The photograph is a close-up of the affected area. The affected area is the head or neck — 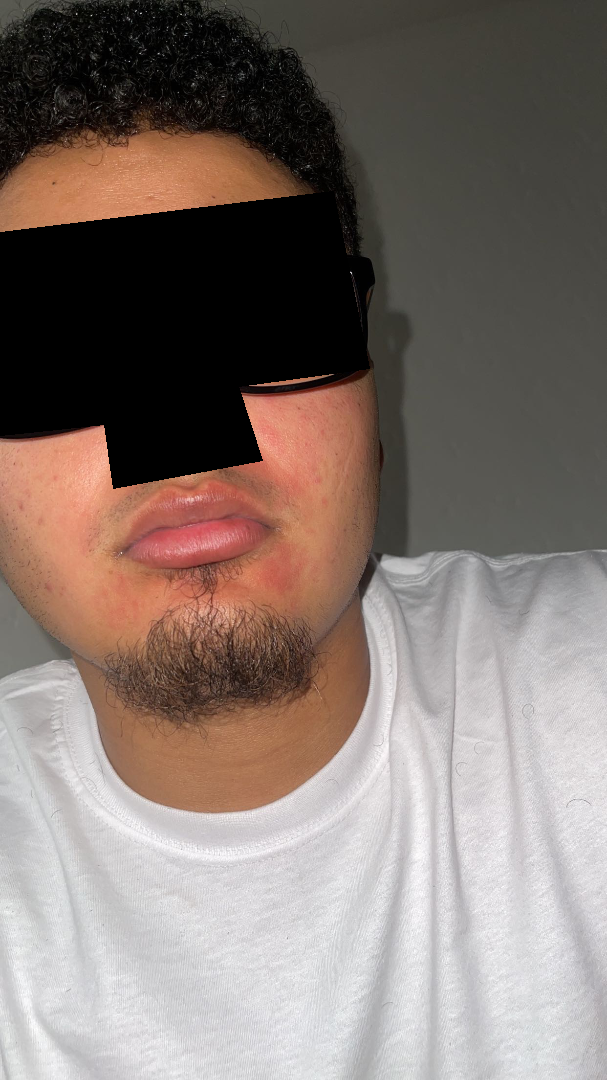History:
The patient considered this a rash. Fitzpatrick skin type III; lay graders estimated Monk skin tone scale 4 (US pool) or 3 (India pool). Symptoms reported: bothersome appearance. The patient notes the lesion is flat. The patient notes the condition has been present for three to twelve months.
Impression:
On photographic review by a dermatologist, Acne (considered); Rosacea (considered); Perioral Dermatitis (considered).